The head or neck is involved; close-up view; the patient described the issue as a rash; the lesion is described as flat and rough or flaky; reported duration is less than one week.
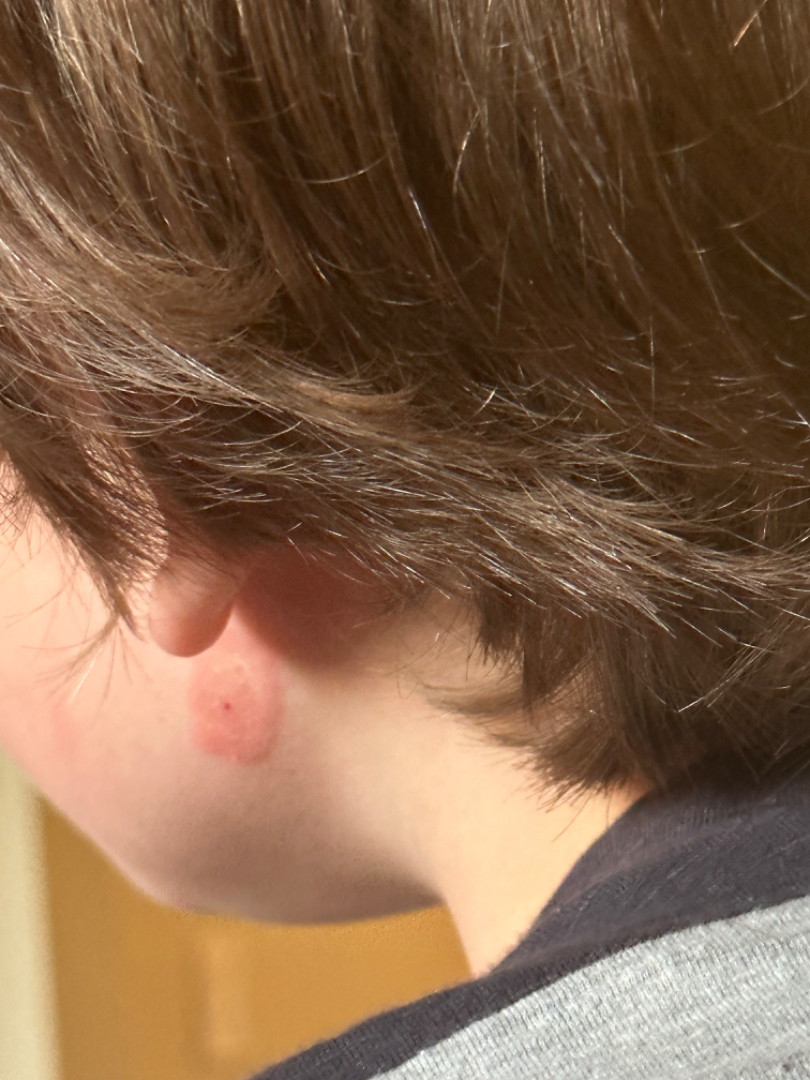assessment — the leading consideration is Eczema